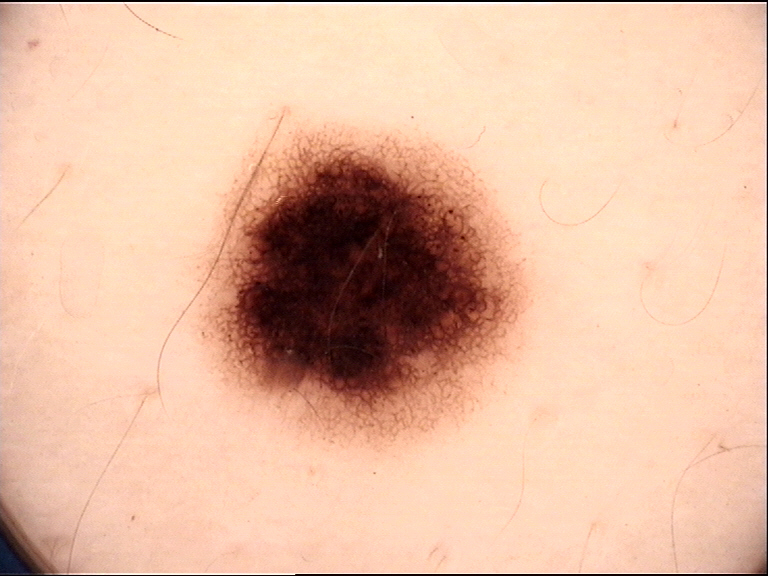| feature | finding |
|---|---|
| label | dysplastic junctional nevus (expert consensus) |